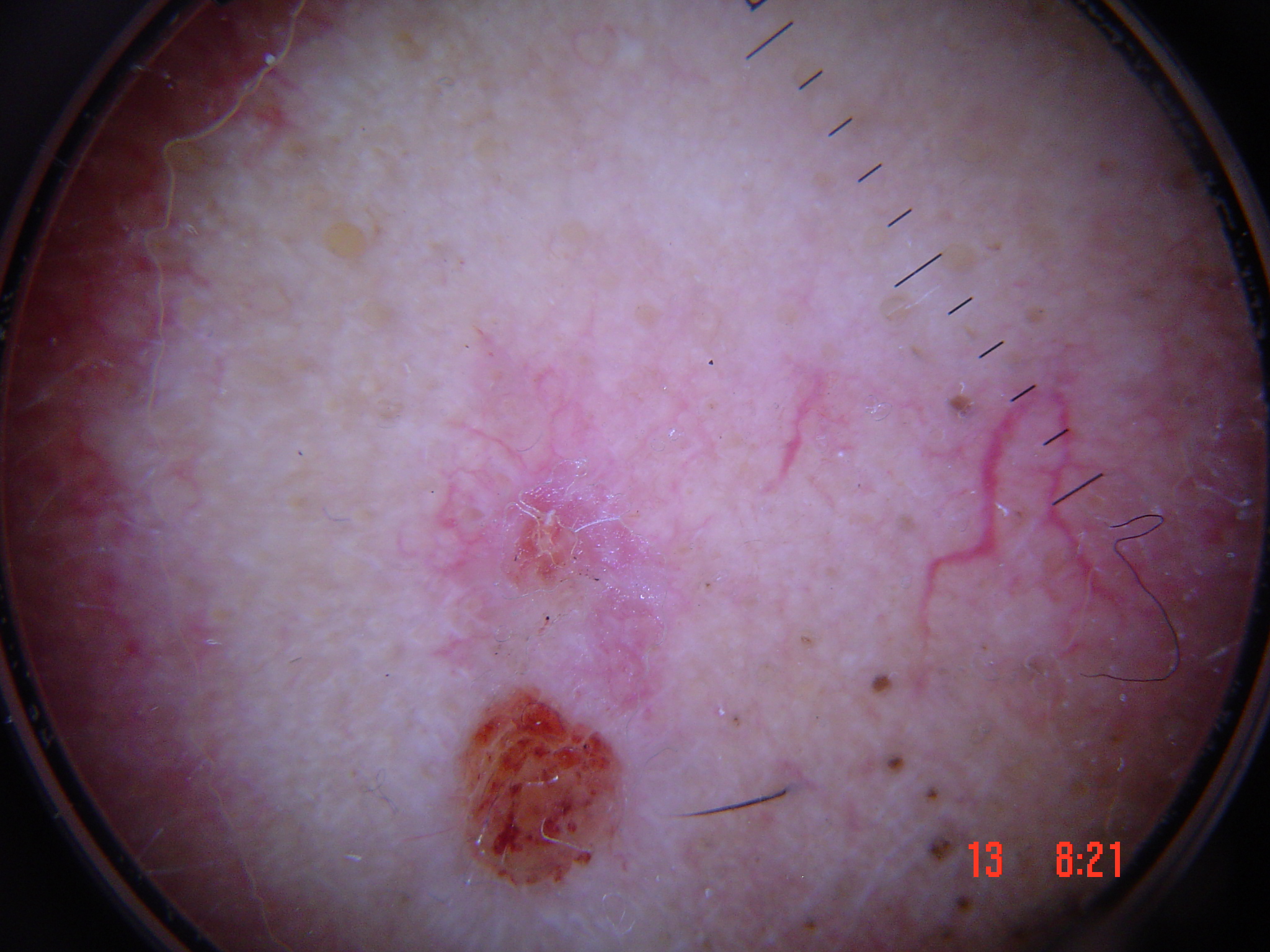Histopathologically confirmed as a squamous cell carcinoma.